A dermoscopic image of a skin lesion.
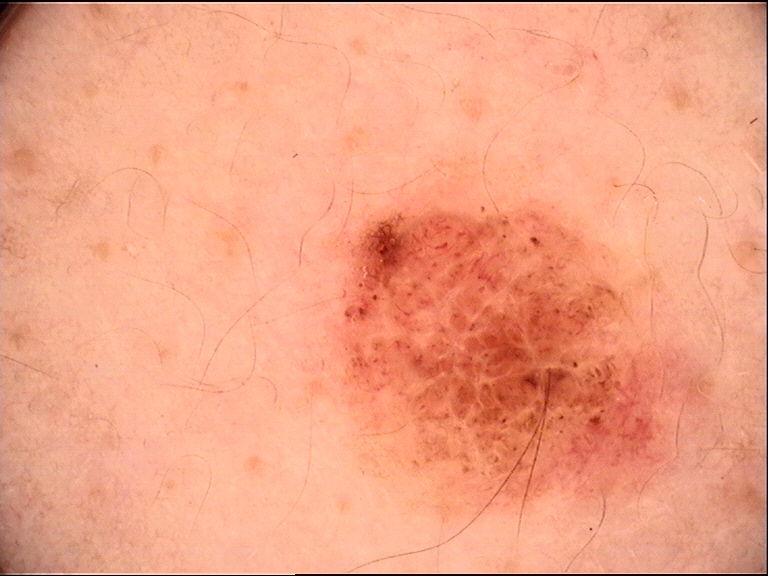Q: What was the diagnostic impression?
A: dysplastic compound nevus (expert consensus)